A female subject 20 years old — 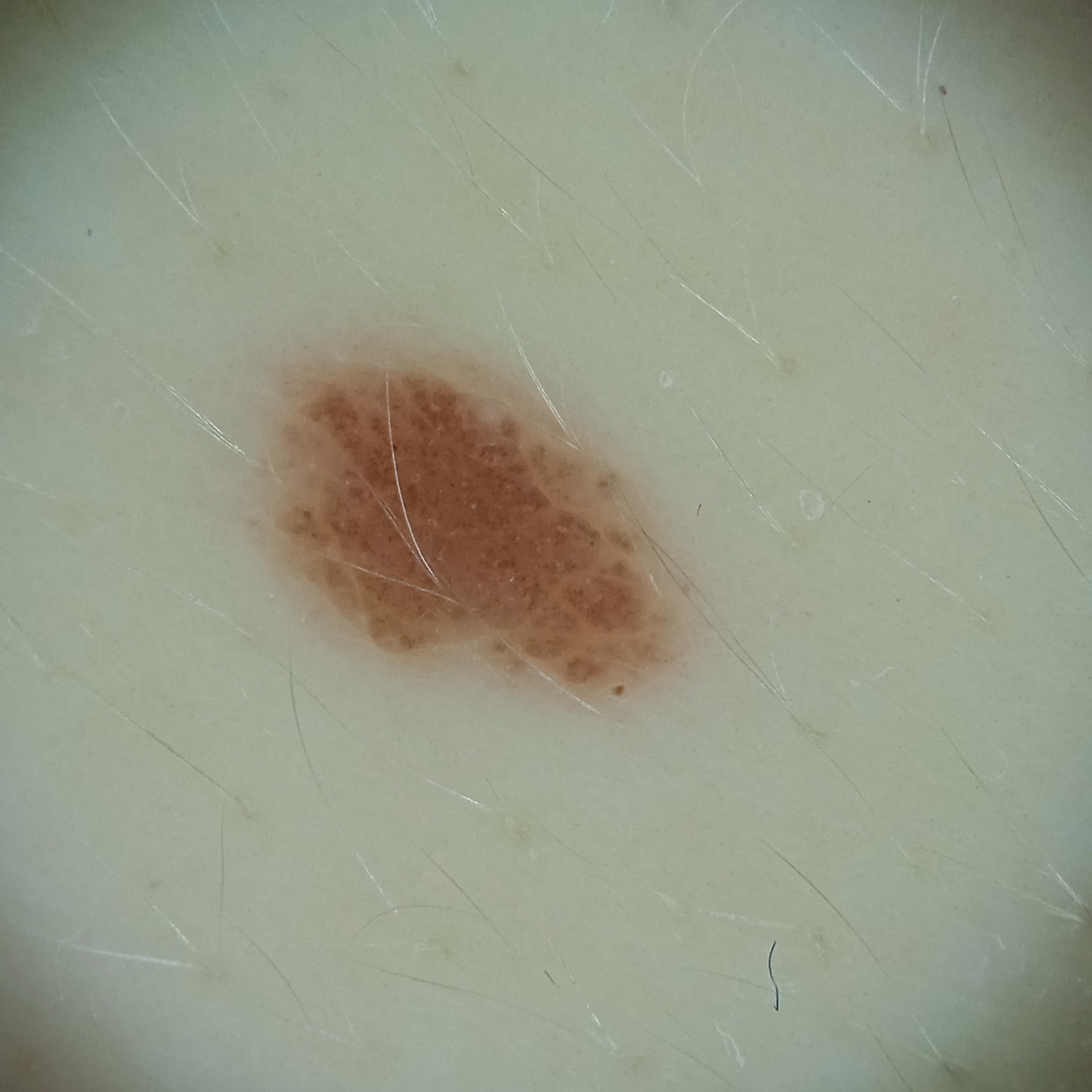Case summary:
The lesion measures approximately 5.1 mm.
Conclusion:
On independent review by four dermatologists, the agreed diagnosis was a melanocytic nevus; there was some disagreement among the reviewers.